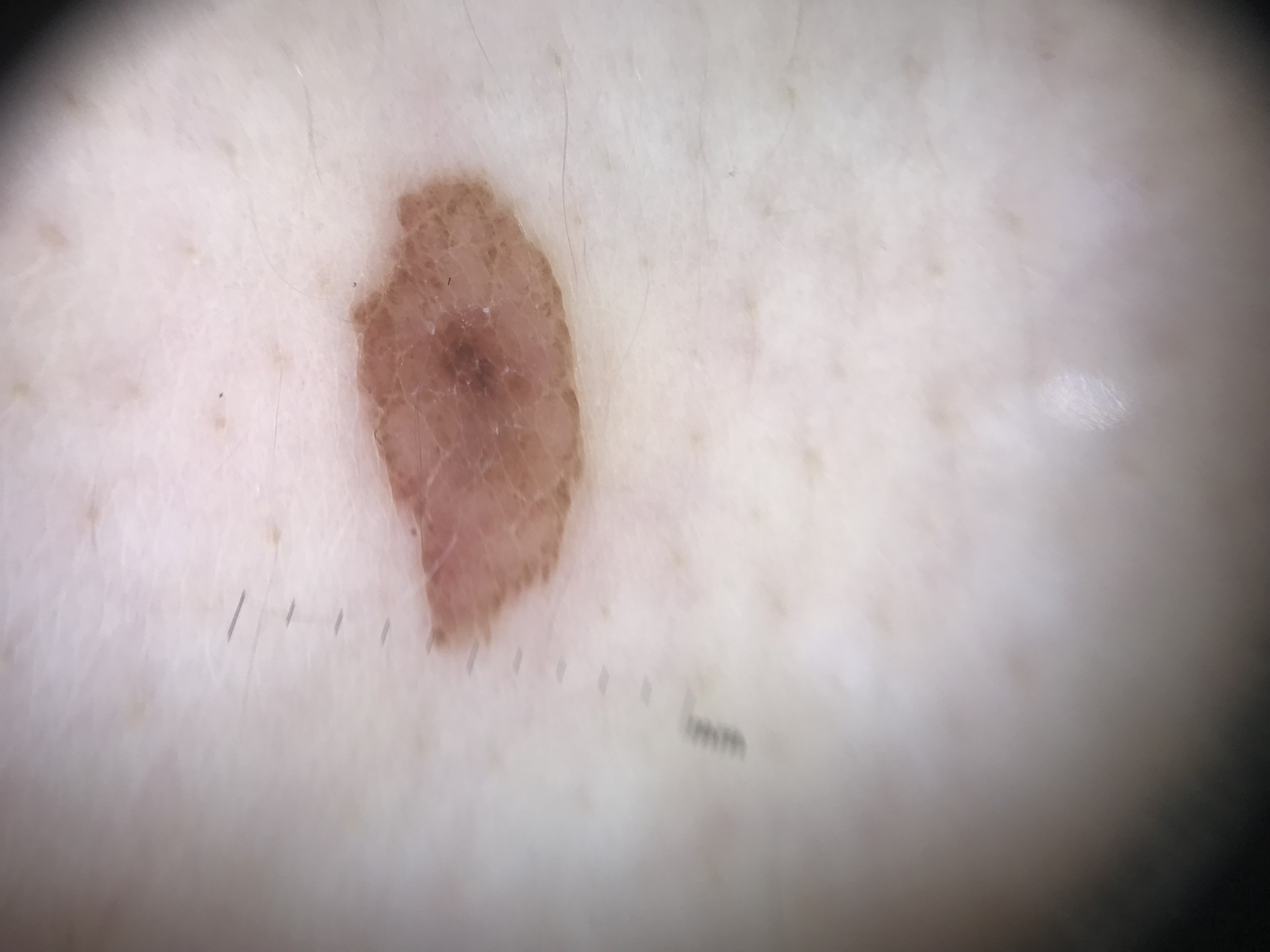Impression:
Consistent with a dysplastic compound nevus.